An image taken at an angle:
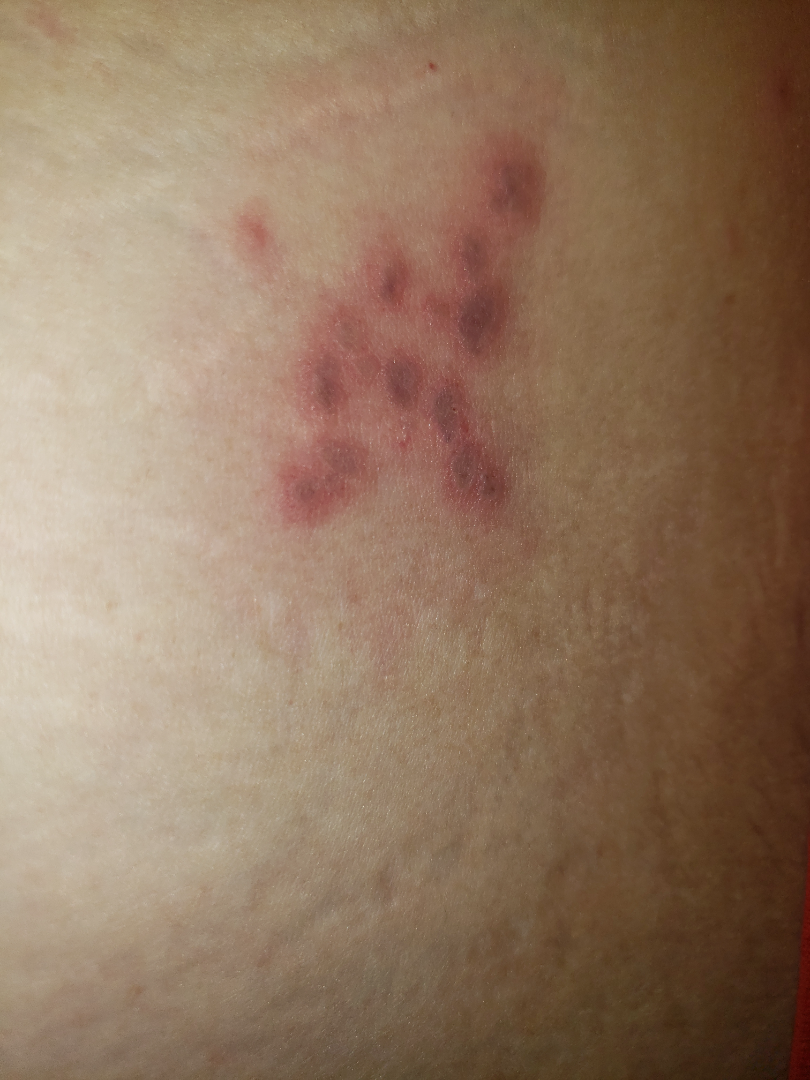Findings: Reviewed remotely by one dermatologist: the leading consideration is Herpes Simplex; also on the differential is Herpes Zoster.